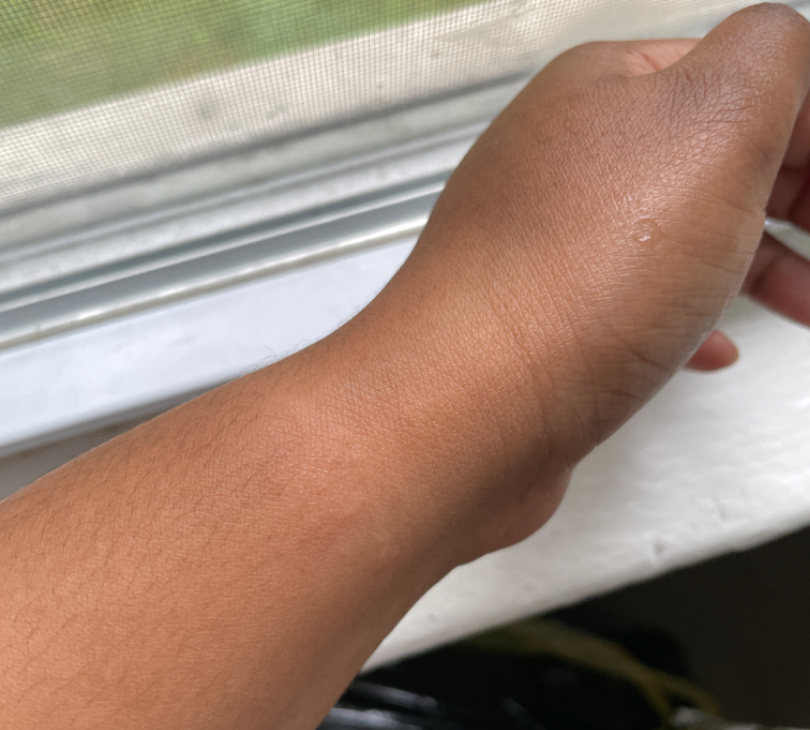On remote review of the image: the differential, in no particular order, includes Contact dermatitis, Eczema and Acute and chronic dermatitis; less probable is Allergic Contact Dermatitis.